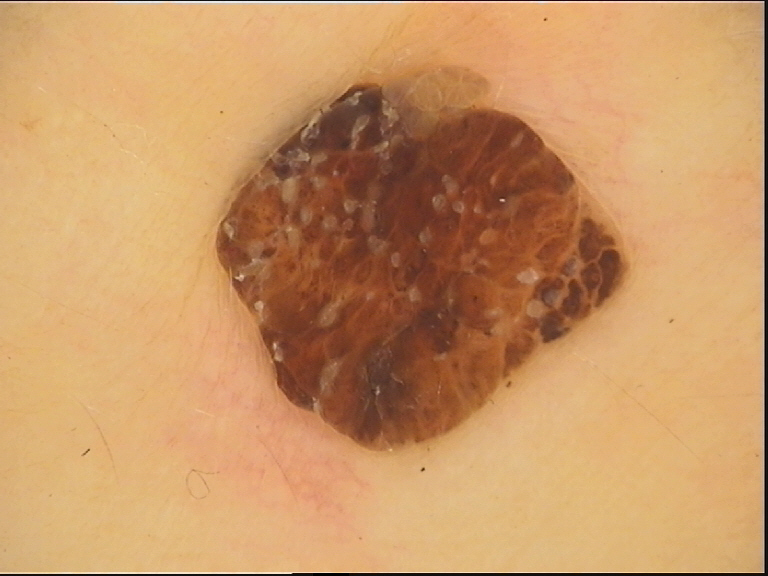Findings: Dermoscopy of a skin lesion. This is a banal lesion. Conclusion: Labeled as a compound nevus.